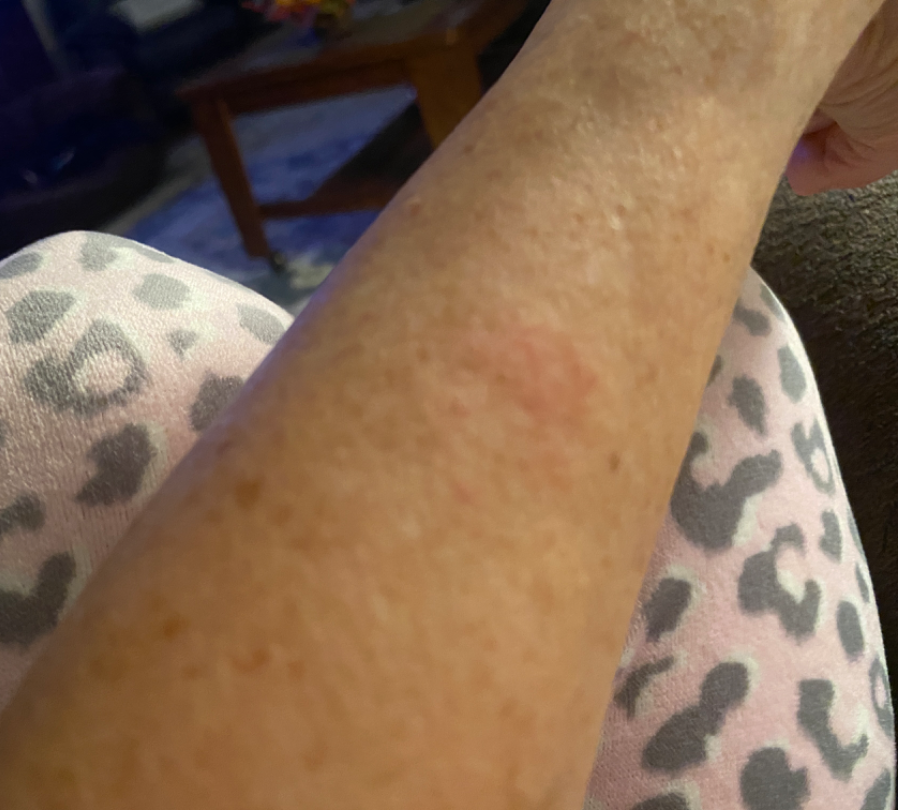Assessment: The skin findings could not be characterized from the image. Clinical context: No associated systemic symptoms reported. Close-up view. The patient indicates the lesion is flat. The arm is involved. The patient described the issue as a rash. The lesion is associated with bothersome appearance. Reported duration is less than one week.